Dermoscopy of a skin lesion:
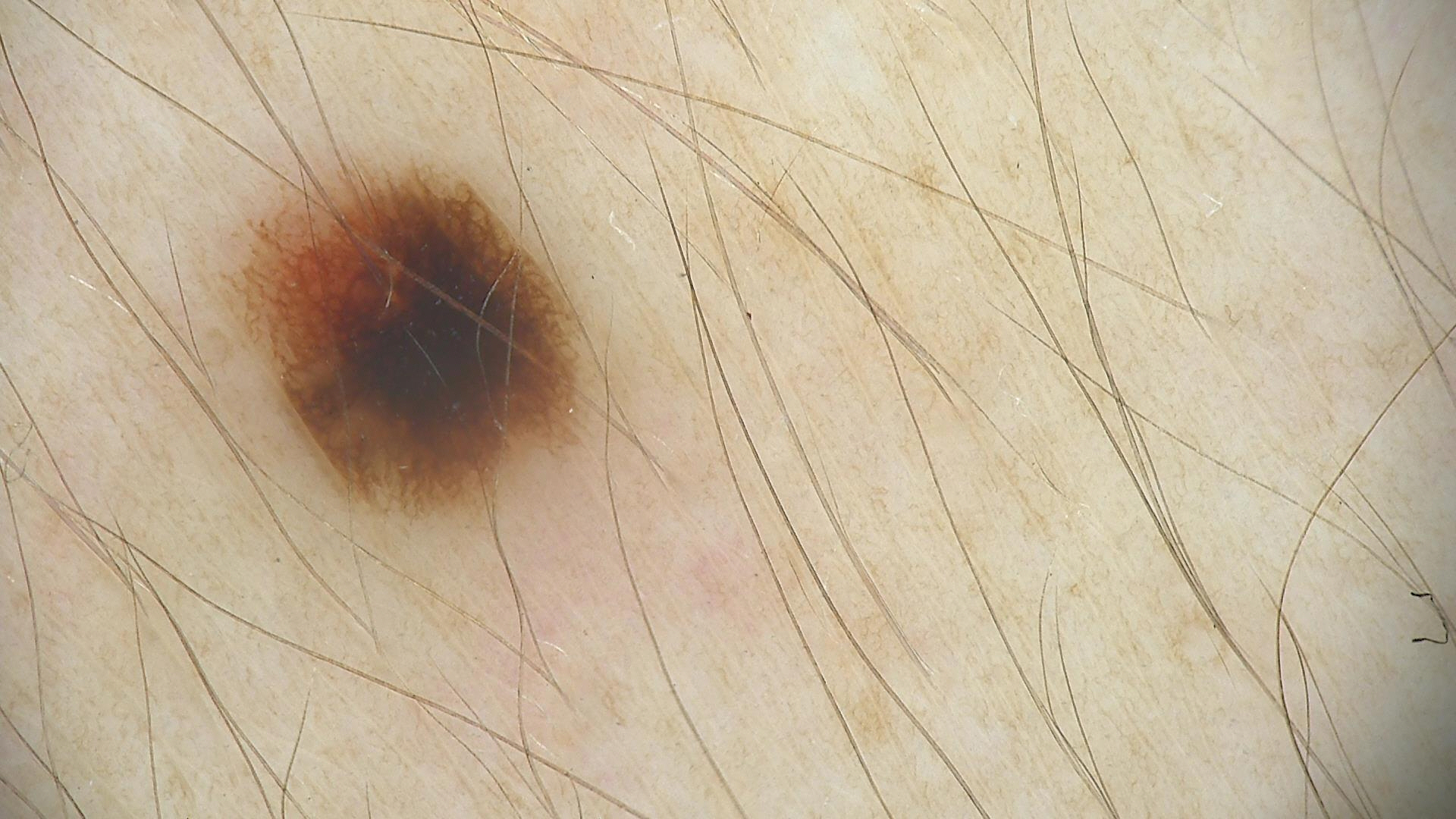diagnosis: dysplastic junctional nevus (expert consensus).